Dermoscopy of a skin lesion.
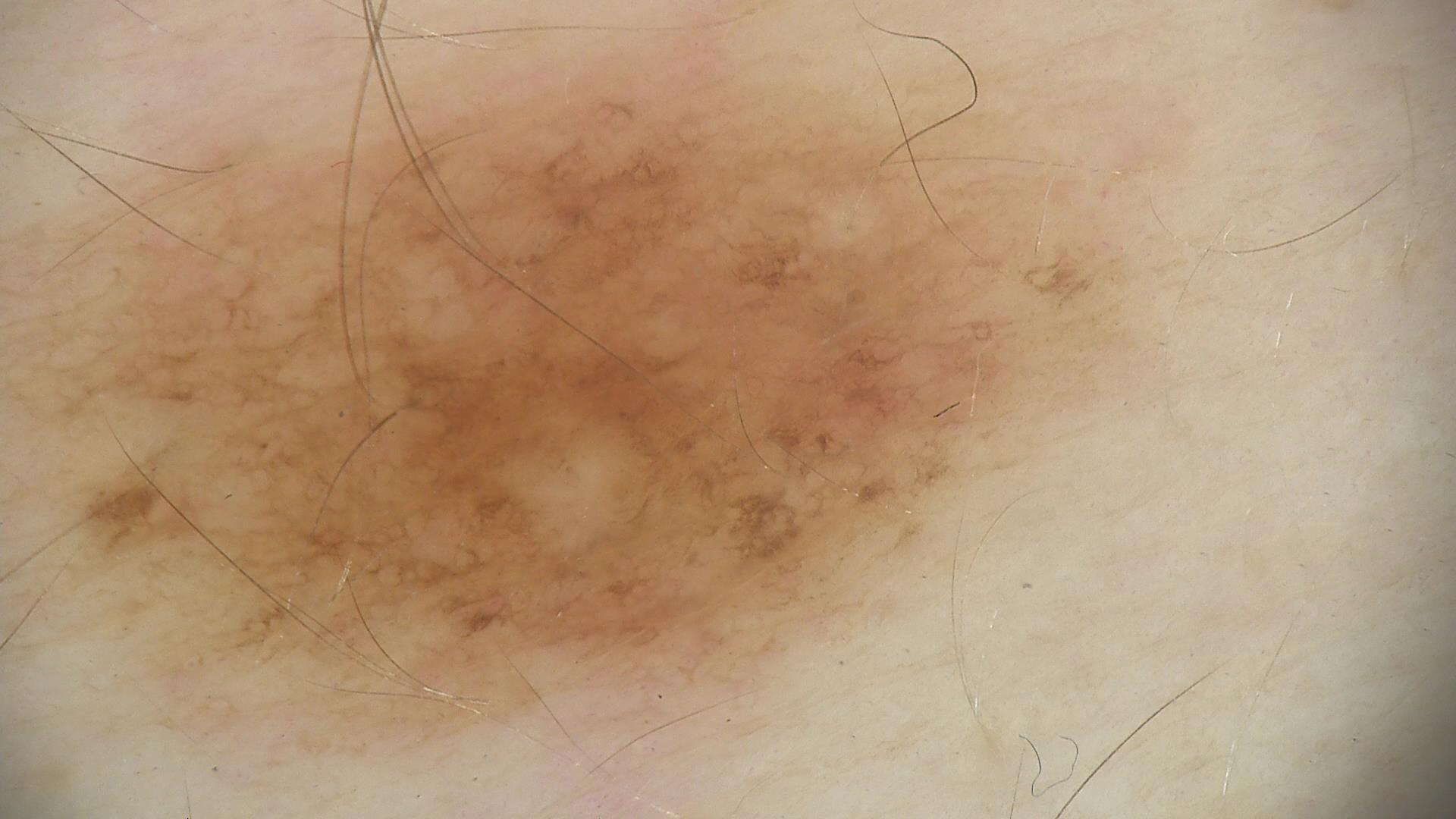Conclusion: Diagnosed as a benign lesion — a dysplastic junctional nevus.